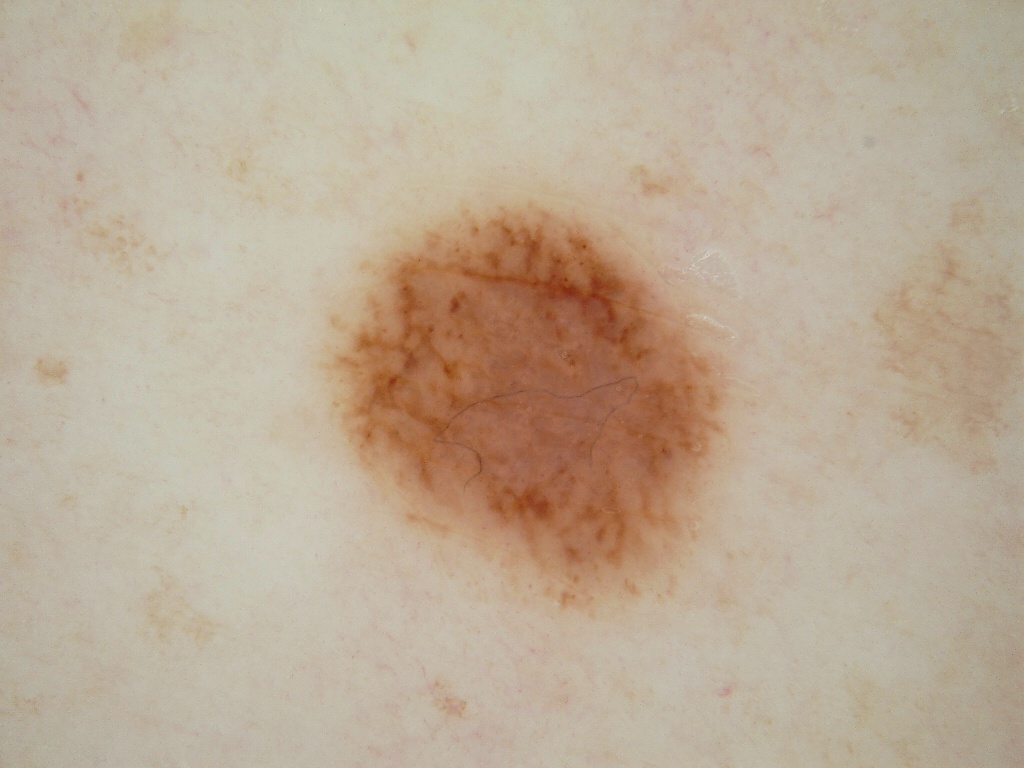  patient:
    sex: female
    age_approx: 40
  image:
    modality: dermoscopy
  dermoscopic_features:
    present:
      - pigment network
      - globules
    absent:
      - milia-like cysts
      - negative network
      - streaks
  lesion_location:
    bbox_xyxy:
      - 320
      - 185
      - 748
      - 618
  diagnosis:
    name: melanocytic nevus
    malignancy: benign
    lineage: melanocytic
    provenance: clinical